A subject in their 30s. A clinical close-up photograph of a skin lesion:
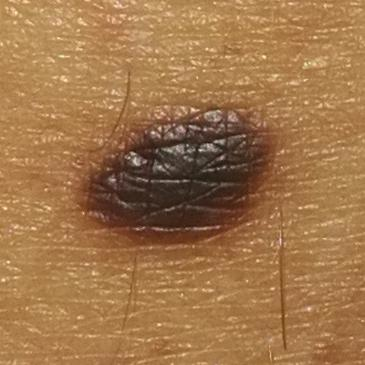Case summary:
The lesion involves a thigh. The patient describes that the lesion is elevated.
Conclusion:
Clinically diagnosed as a benign skin lesion — a nevus.